A dermoscopic photograph of a skin lesion: 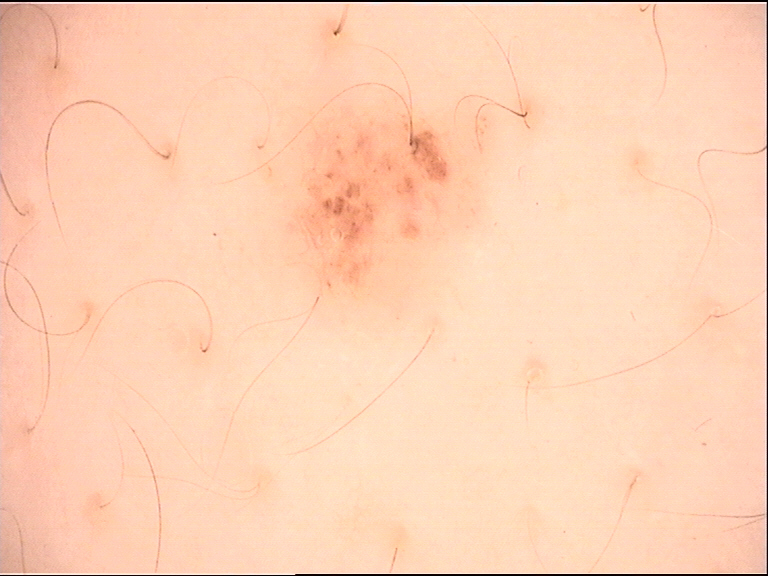The morphology is that of a banal lesion.
Classified as a compound nevus.